A dermoscopic close-up of a skin lesion: 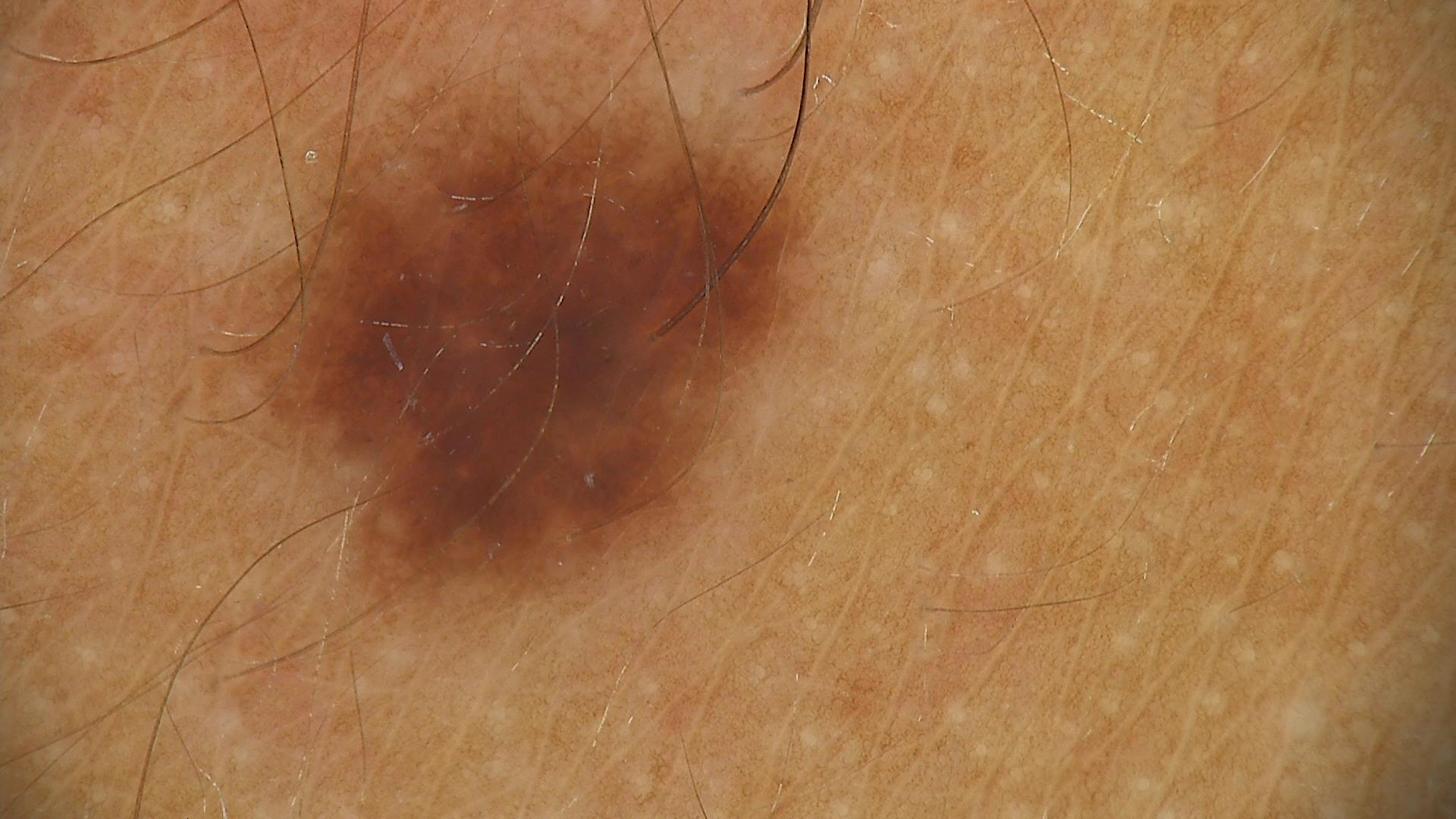The diagnosis was a dysplastic junctional nevus.